Fitzpatrick skin type II · a male patient about 85 years old or older · the chart records a previous melanoma · a clinical photograph of a skin lesion — 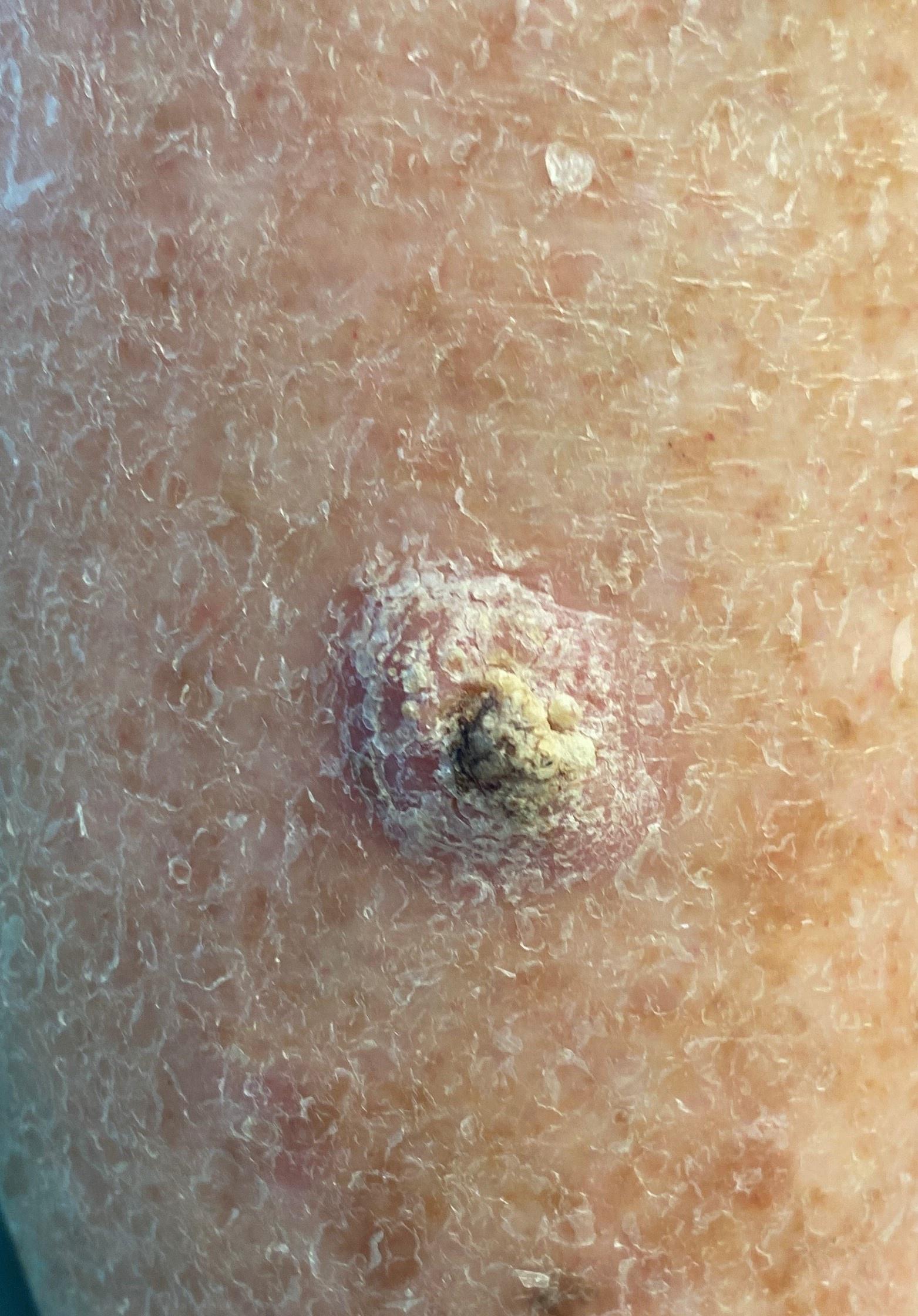Case summary: The lesion is located on a lower extremity. Diagnosis: Biopsy-confirmed as a lesion of epidermal origin — a squamous cell carcinoma.